The subject is 18–29, female · the arm is involved · the photograph is a close-up of the affected area: 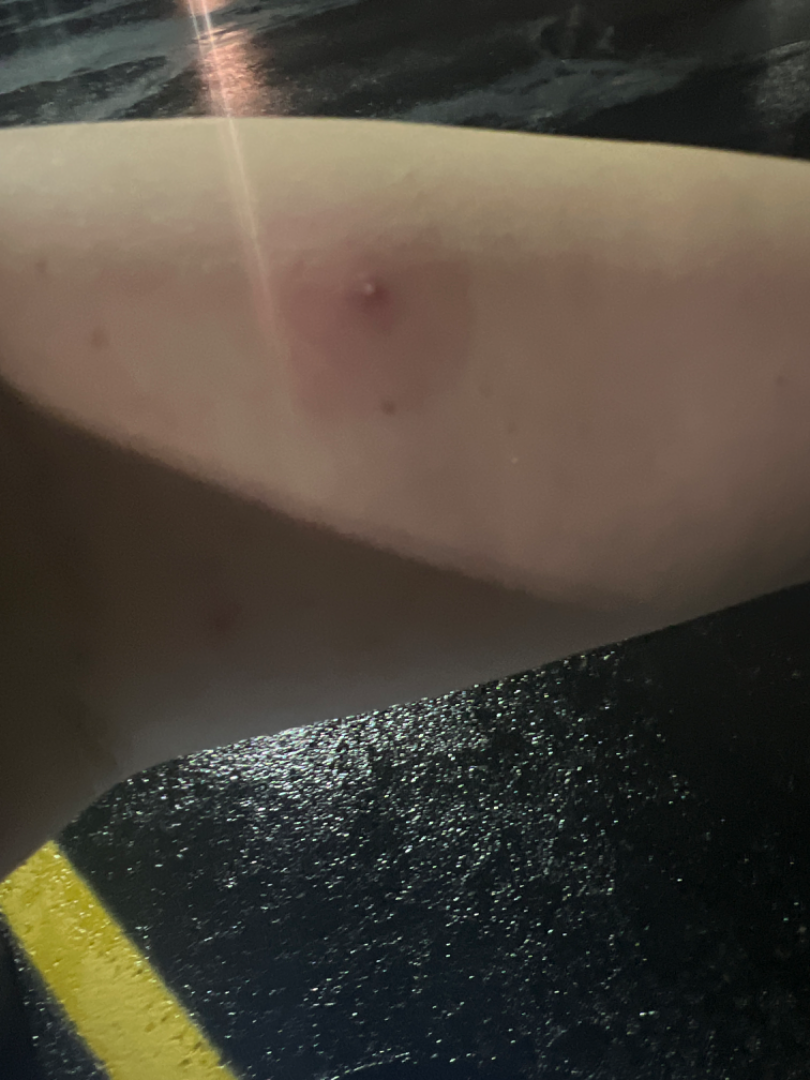On remote dermatologist review: most consistent with pustules; also consider Abscess; also on the differential is Insect Bite.